Located on the leg; this is a close-up image:
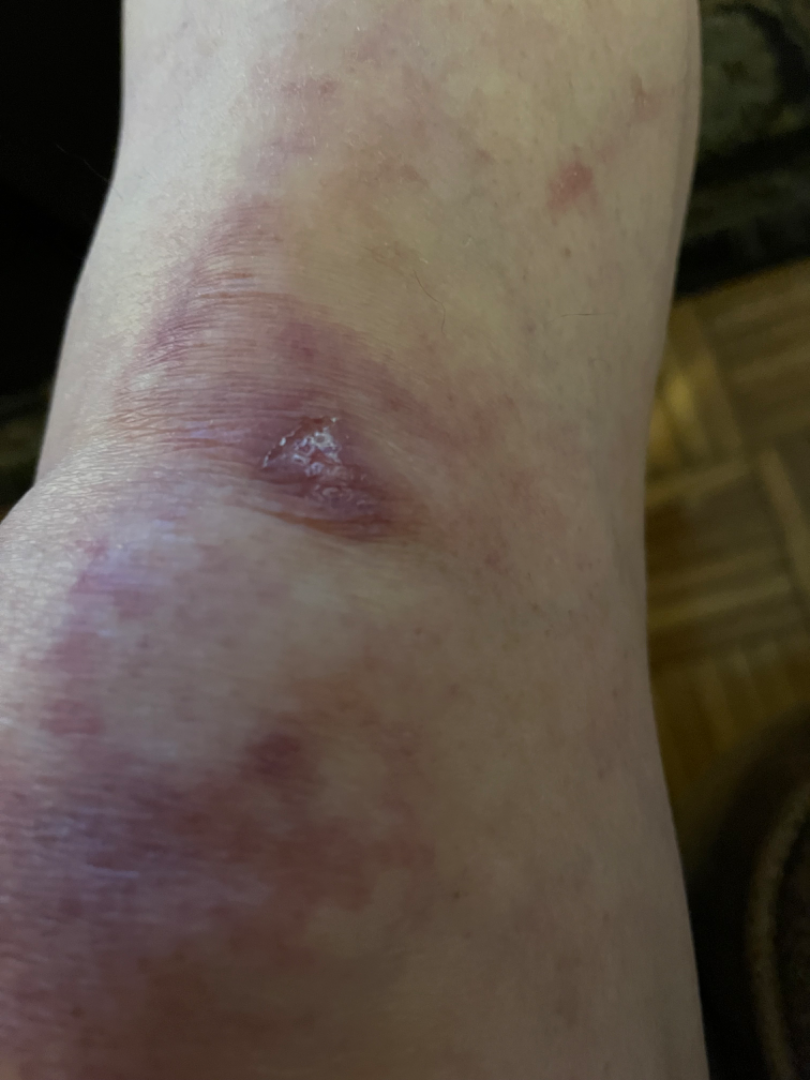The condition could not be reliably identified from the image. Reported lesion symptoms include darkening and bothersome appearance.